A close-up photograph; located on the leg; symptoms reported: pain, enlargement, bothersome appearance, itching and darkening; female contributor, age 40–49; the condition has been present for three to twelve months; the patient reported no systemic symptoms; Fitzpatrick phototype II: 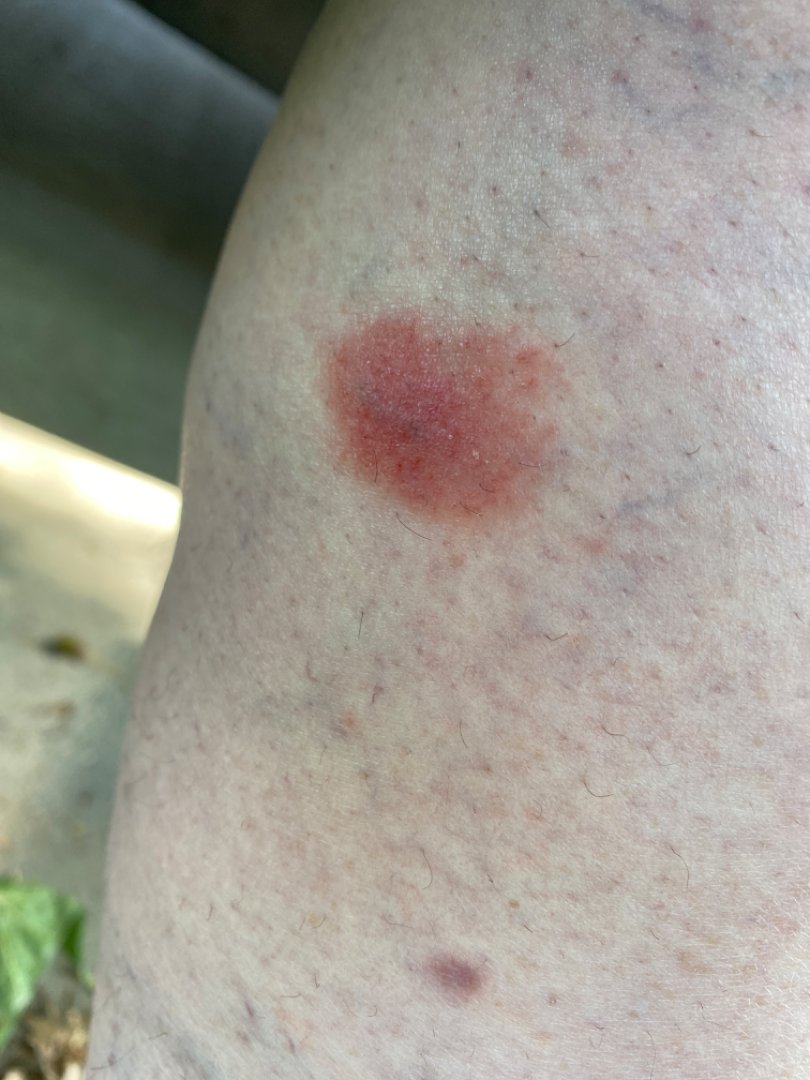Impression: Three dermatologists independently reviewed the case: favoring Pigmented purpuric eruption; also consider Eczema; with consideration of Allergic Contact Dermatitis; less likely is Localized cutaneous vasculitis; less probable is Necrobiosis lipoidica.